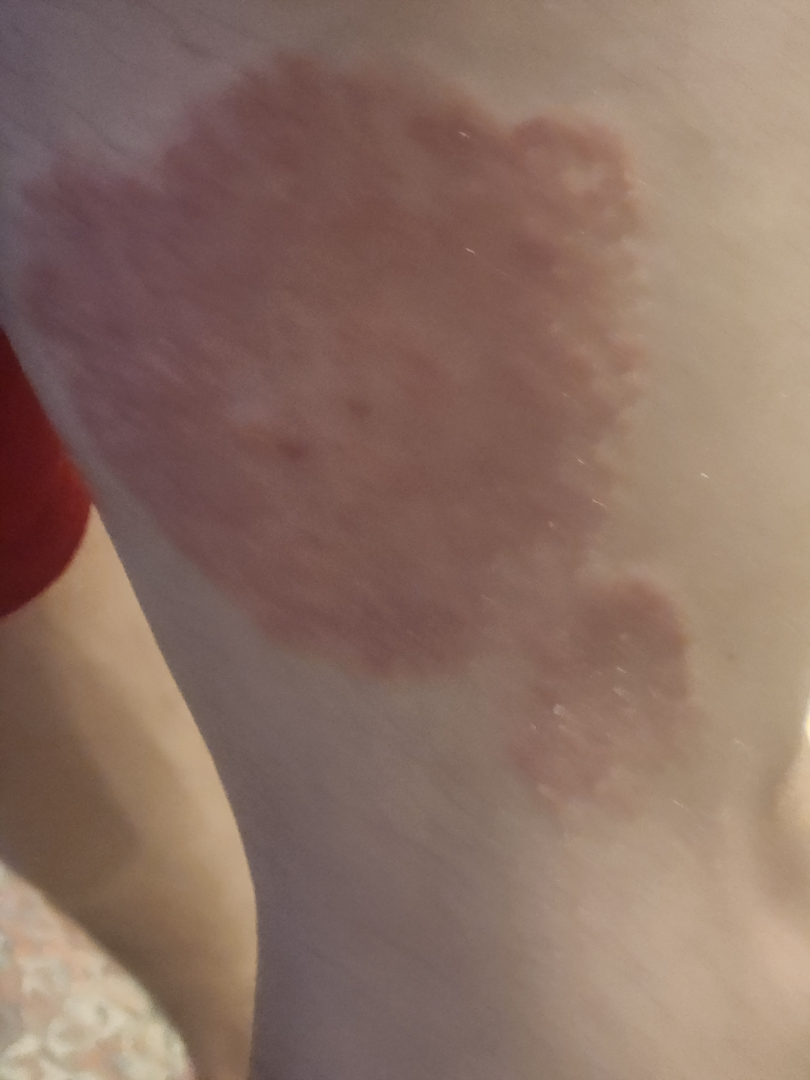The leading consideration is Psoriasis; the differential also includes Eczema.